The subject is female · self-categorized by the patient as a rash · reported lesion symptoms include itching, burning, bothersome appearance, pain and enlargement · the lesion is described as fluid-filled and raised or bumpy · the lesion involves the arm · this image was taken at an angle.
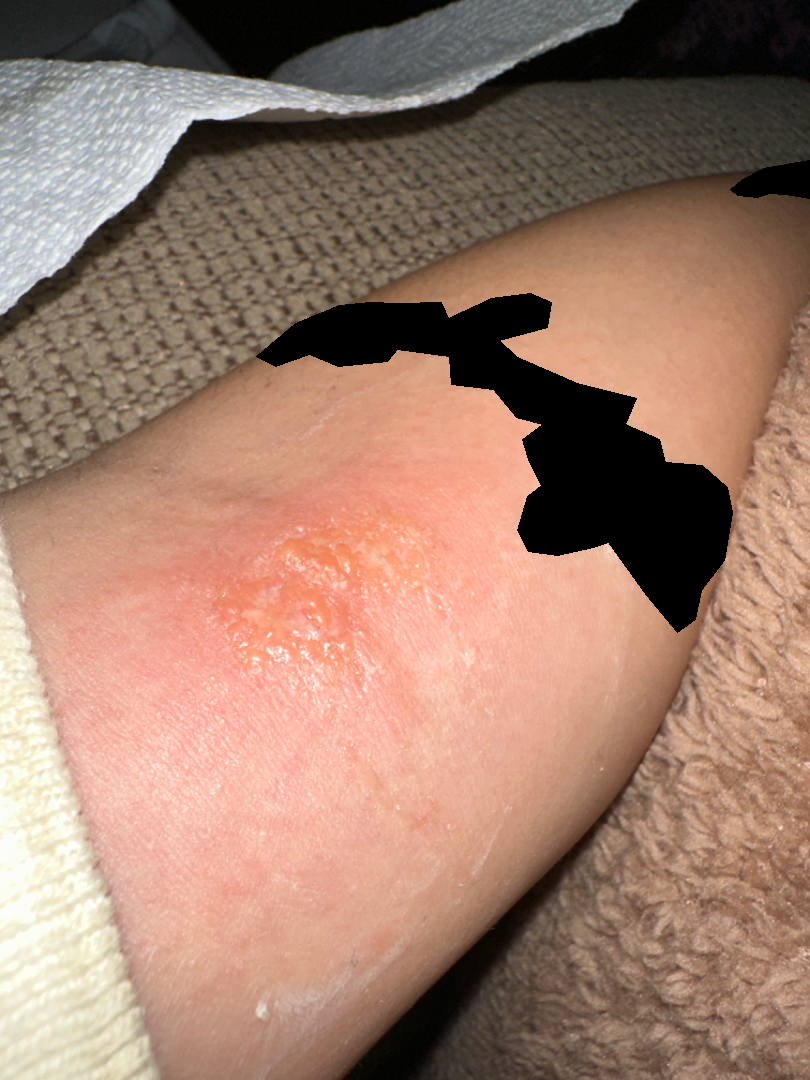{"differential": {"leading": ["Eczema"], "considered": ["Allergic Contact Dermatitis"]}}